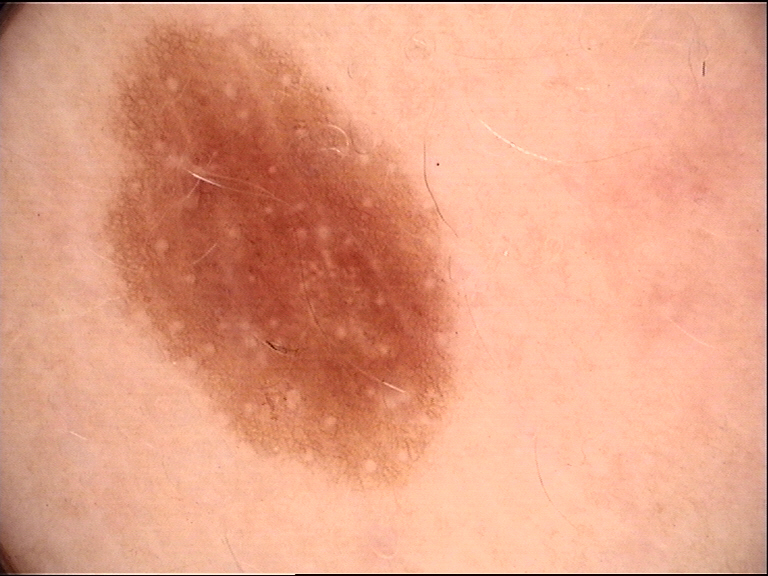Diagnosed as a benign lesion — a dysplastic junctional nevus.